The patient described the issue as a rash · skin tone: Fitzpatrick phototype IV; lay graders estimated a MST of 4 · the patient notes the lesion is raised or bumpy · the patient notes itching · this is a close-up image · located on the front of the torso, back of the torso, leg and arm · the patient notes the condition has been present for less than one week · the subject is 40–49, male.
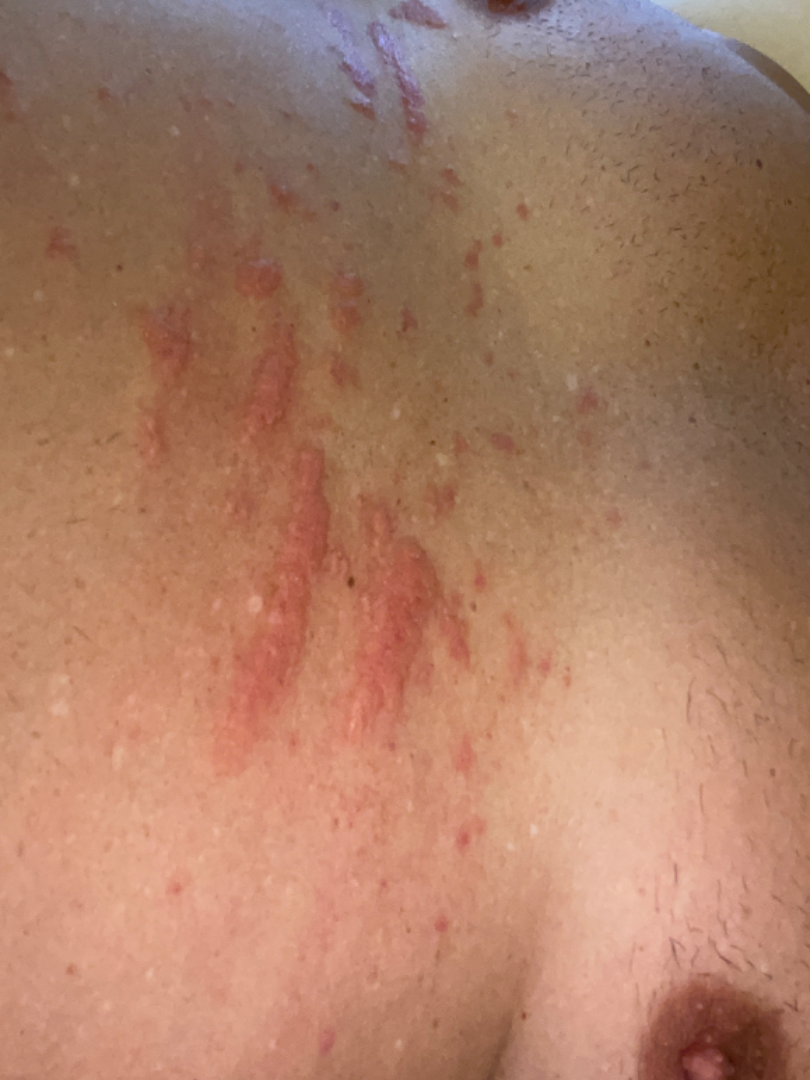<dermatology_case>
  <differential>Allergic Contact Dermatitis</differential>
</dermatology_case>